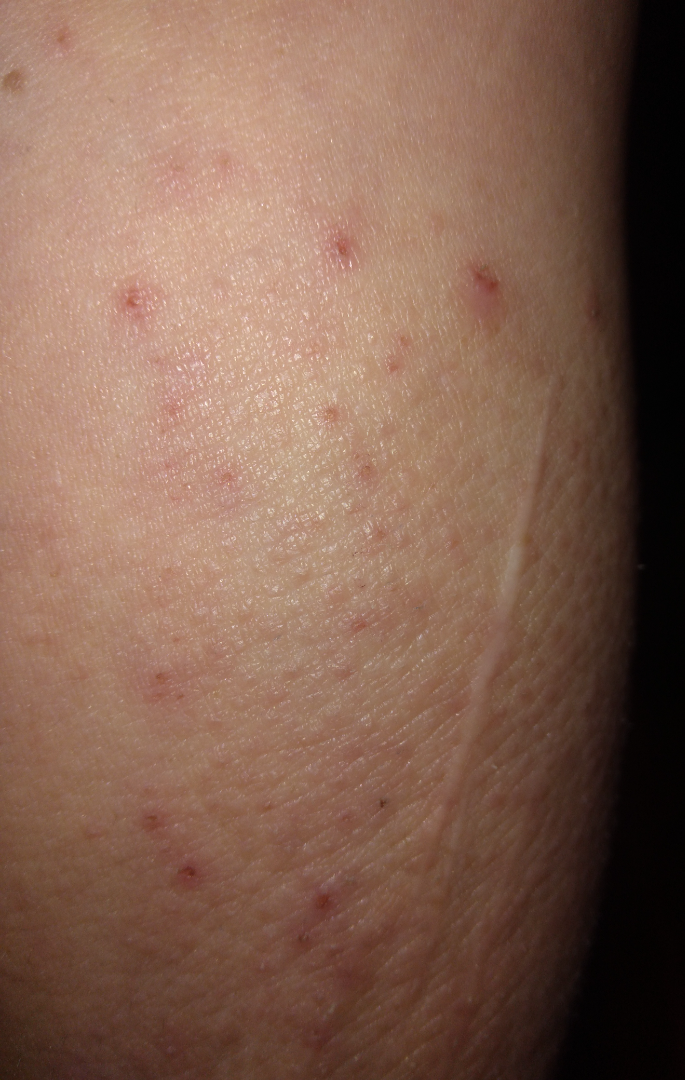{
  "differential": {
    "Lichen Simplex Chronicus": 0.35,
    "Folliculitis": 0.26,
    "Tinea": 0.26,
    "Eczema": 0.13
  }
}